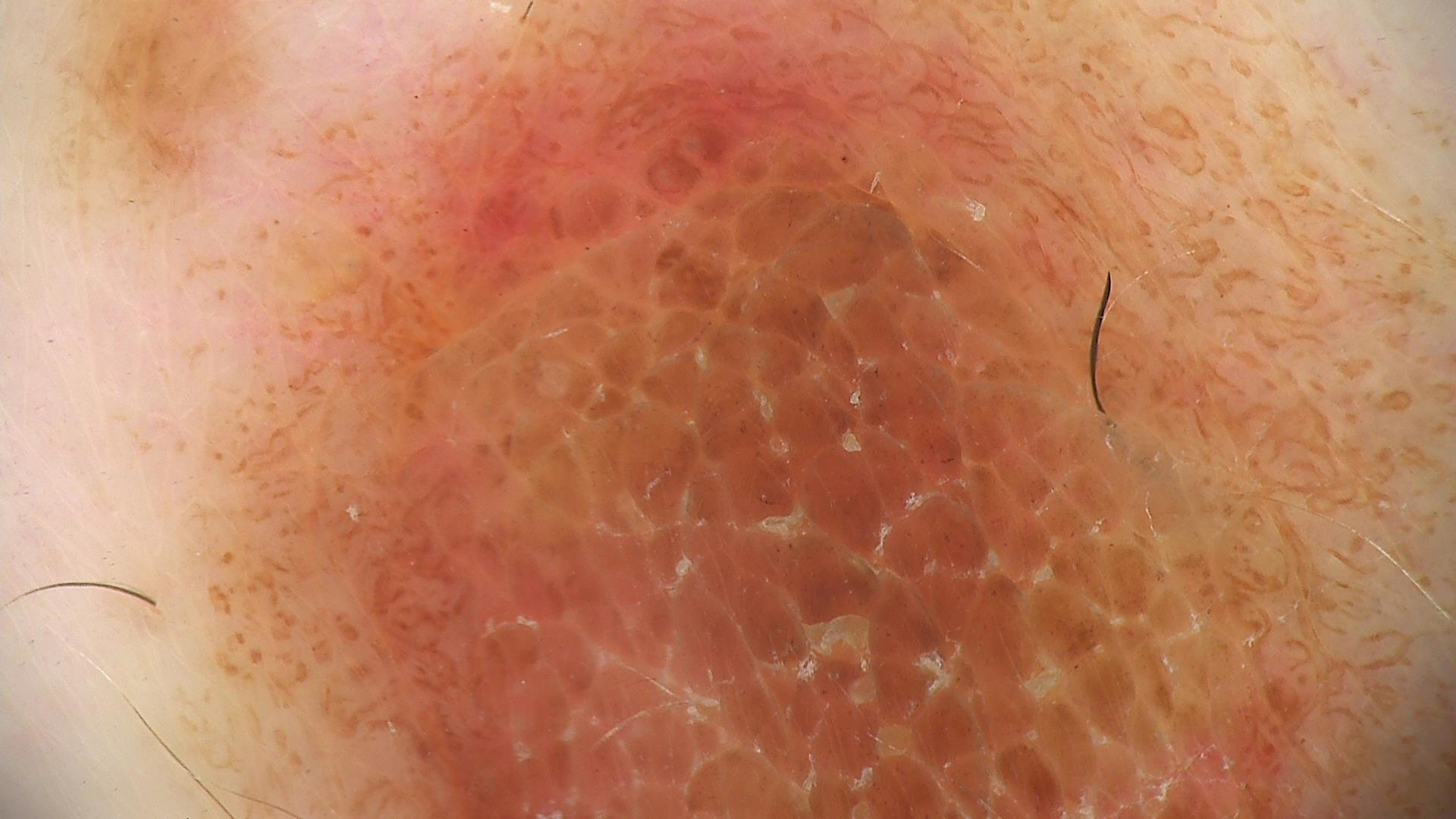Q: What kind of image is this?
A: dermoscopy
Q: What was the diagnostic impression?
A: dysplastic compound nevus (expert consensus)